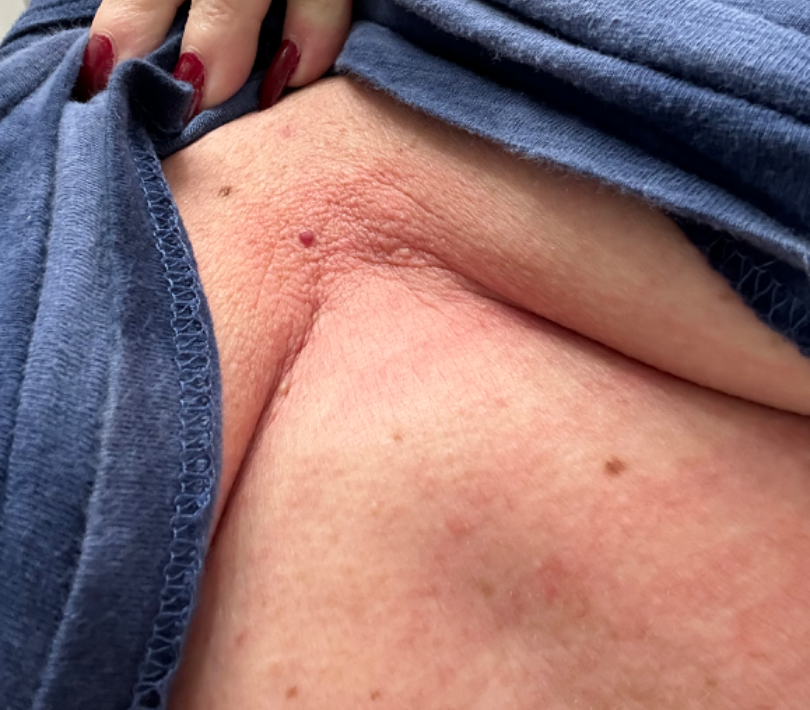impression = most likely Drug Rash; also raised was Eczema